The lesion is described as raised or bumpy and fluid-filled · symptoms reported: burning and itching · close-up view · the patient reports the condition has been present for one to four weeks · the subject is a female aged 50–59 · the patient considered this a rash:
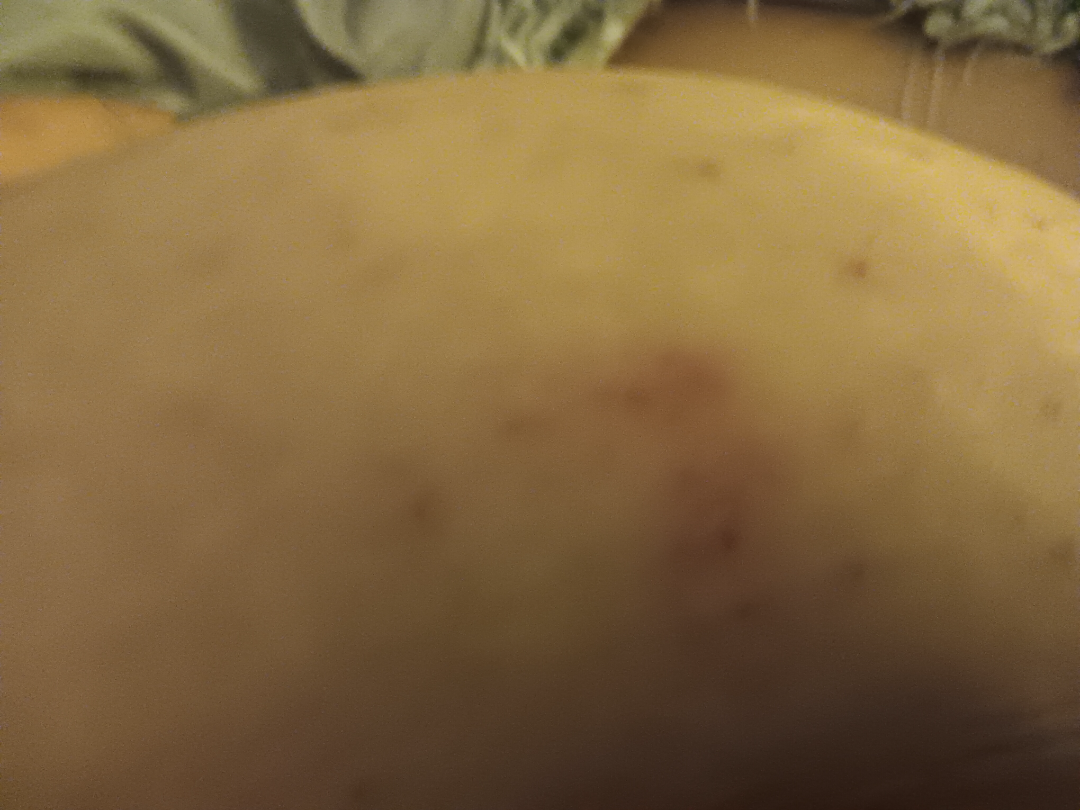assessment = unable to determine.